The patient reports the lesion is raised or bumpy. Reported lesion symptoms include pain. The patient is 30–39, male. The patient considered this a rash. This image was taken at an angle. The patient reports the condition has been present for less than one week: 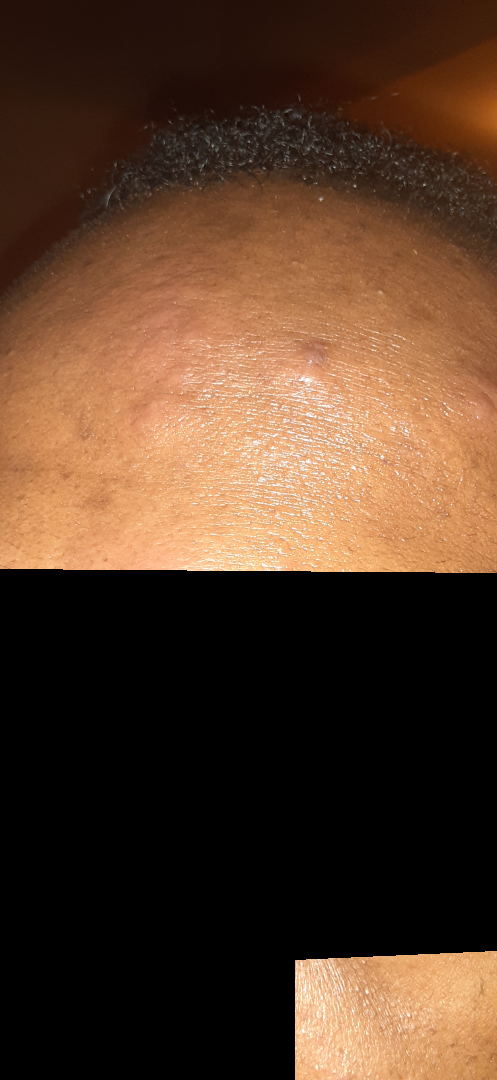Impression:
Three independent reviewers: Pemphigus vulgaris and Acne were each considered, in no particular order.